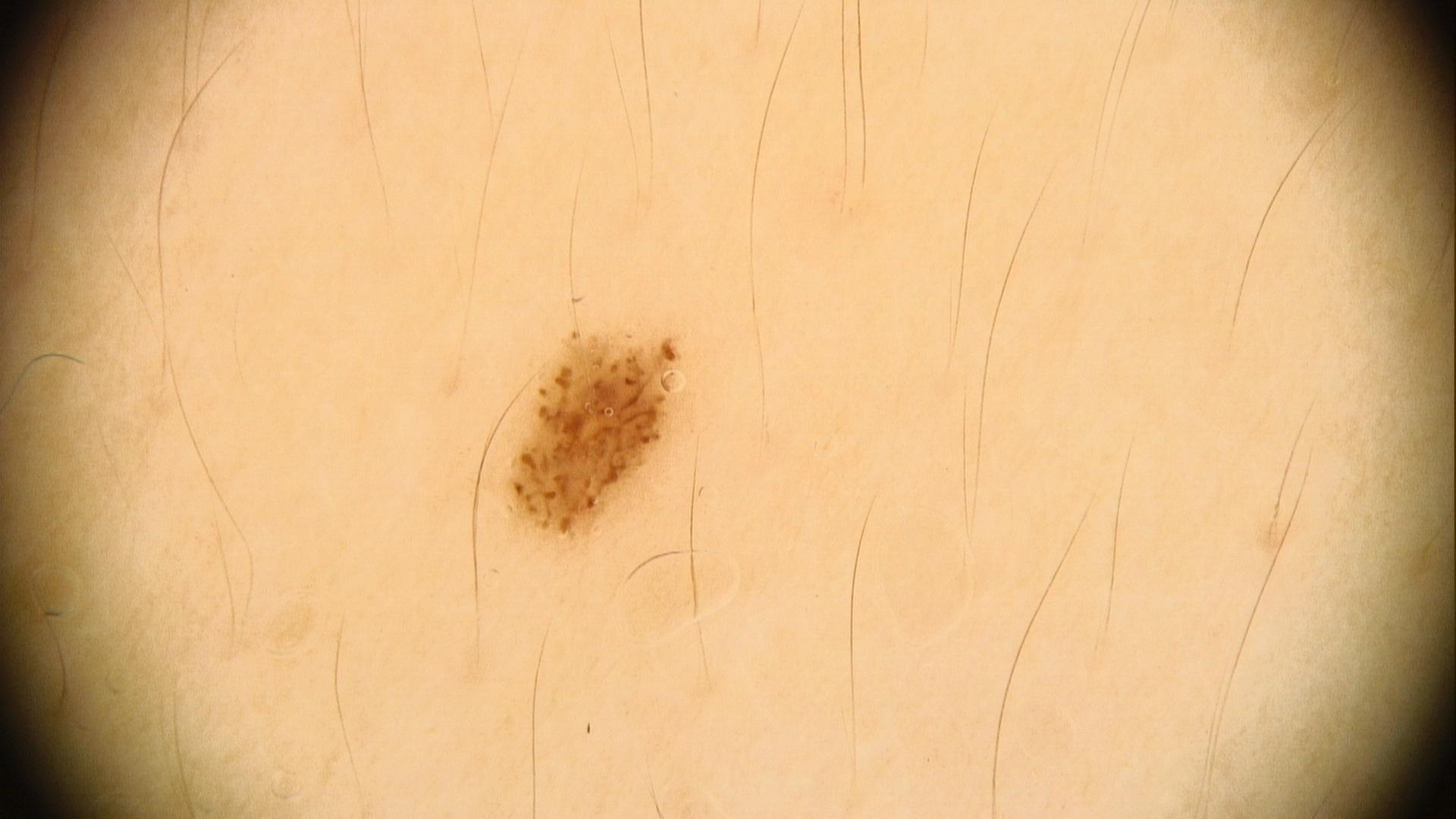A dermatoscopic image of a skin lesion. The lesion involves an upper extremity. Clinically diagnosed as a nevus.